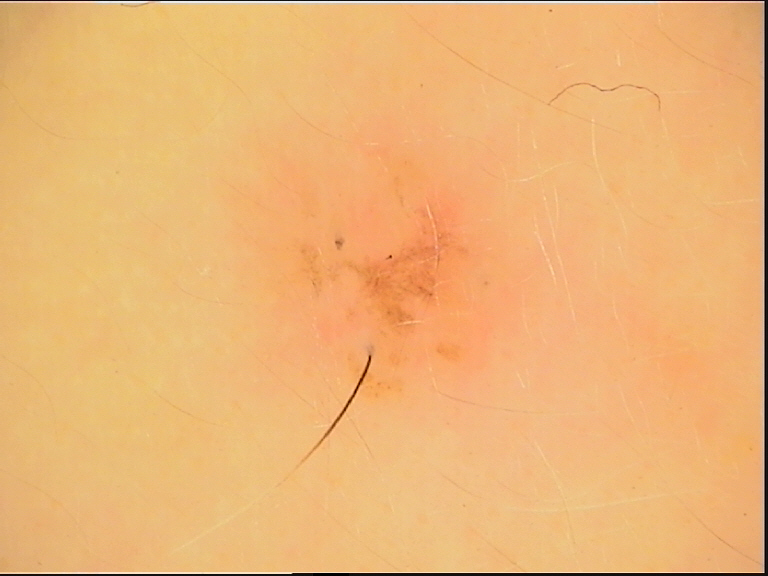Findings:
A dermoscopic close-up of a skin lesion.
Impression:
Consistent with a banal lesion — a compound nevus.